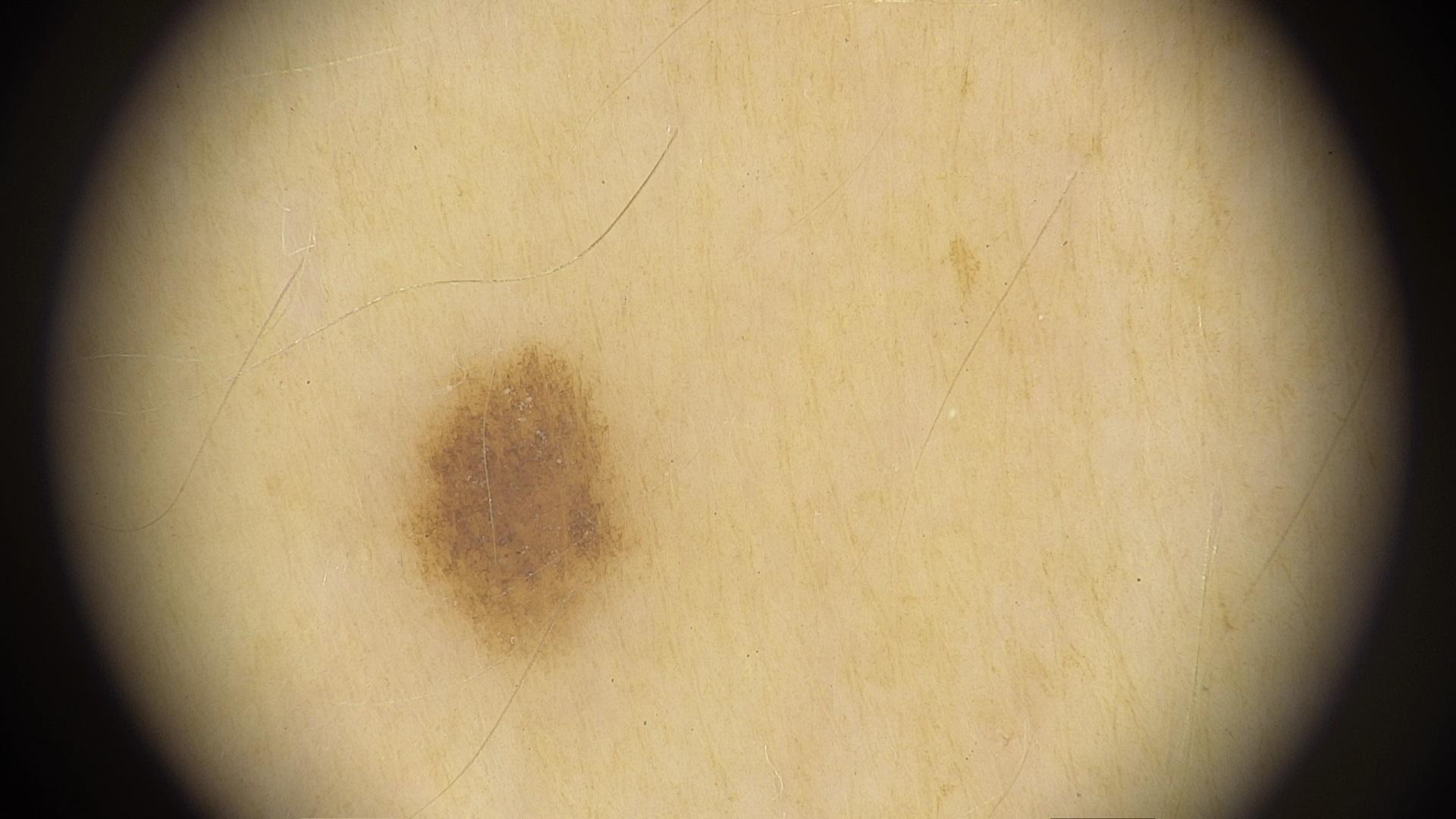The chart documents a prior melanoma. A female patient in their 50s. The diagnostic impression was a nevus.